Located on the head or neck. The subject is 18–29, female. The photograph was taken at an angle — 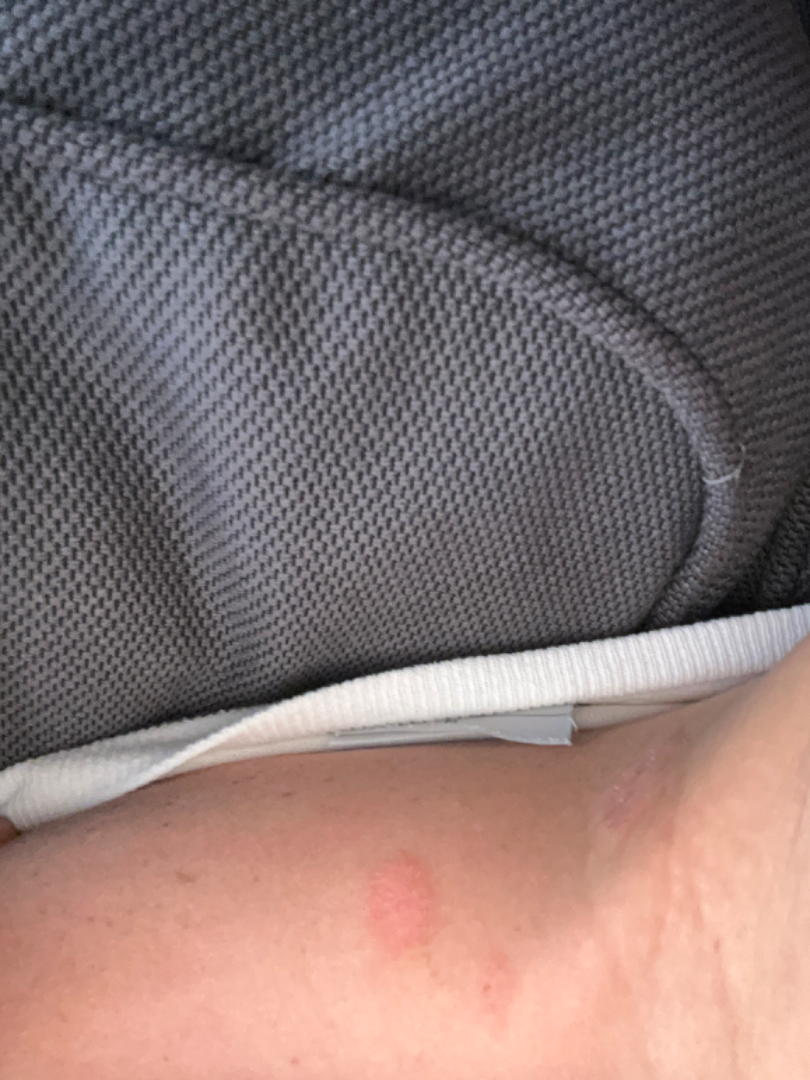{"texture": "rough or flaky", "duration": "one to four weeks", "differential": {"leading": ["Pityriasis rosea"], "considered": ["Eczema"], "unlikely": ["Syphilis"]}}